Female subject, age 40–49. The arm is involved. The photo was captured at a distance.
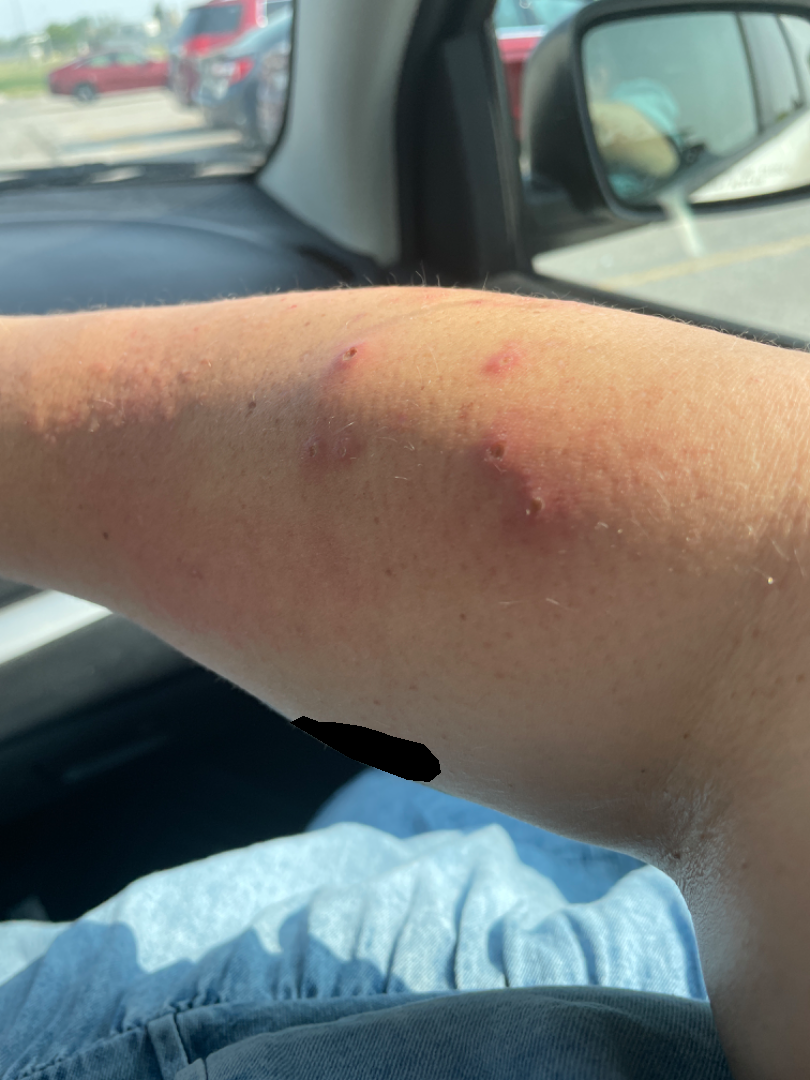assessment = could not be assessed.